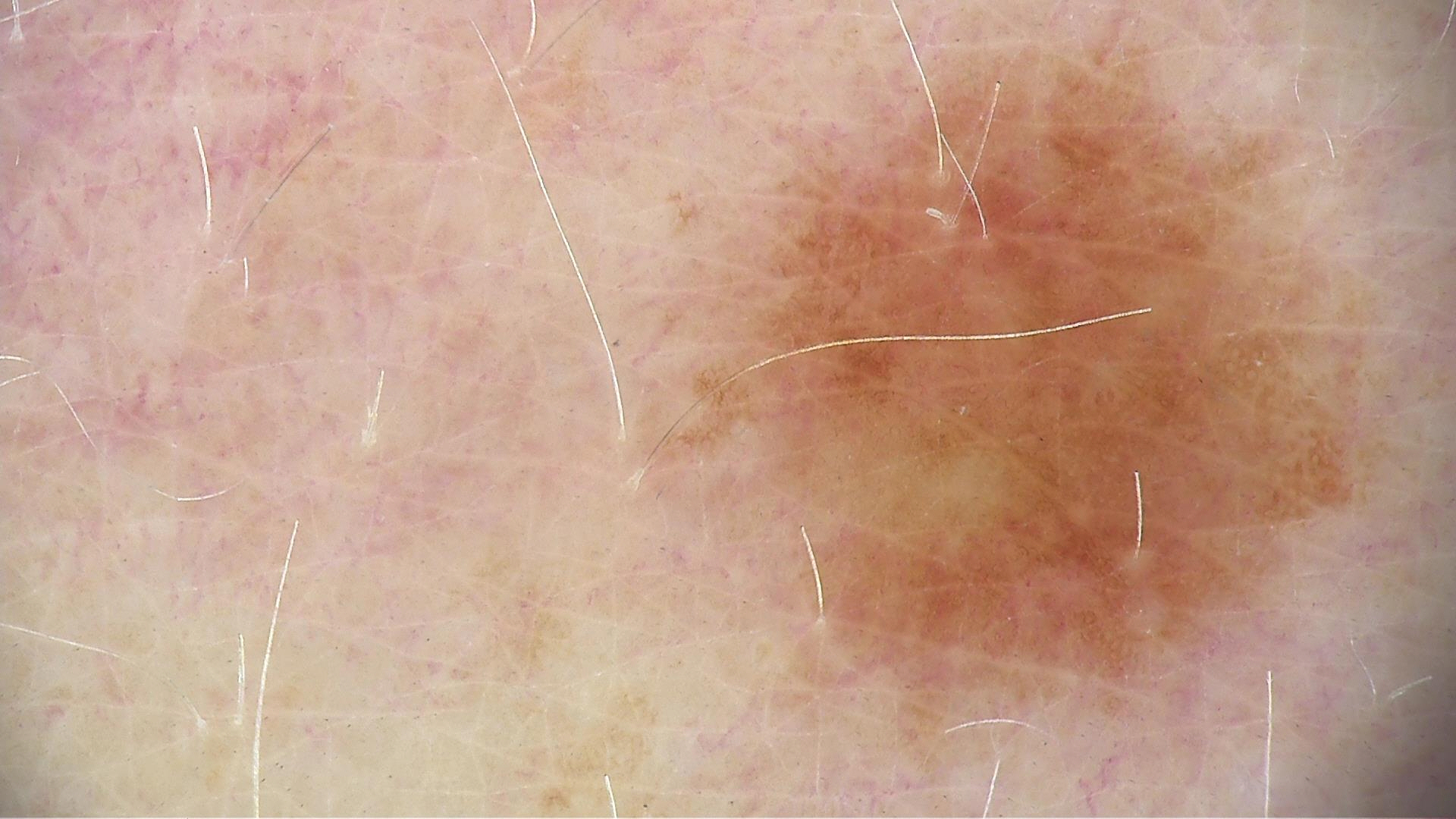Findings: A dermoscopic photograph of a skin lesion. Impression: The diagnosis was a dysplastic junctional nevus.